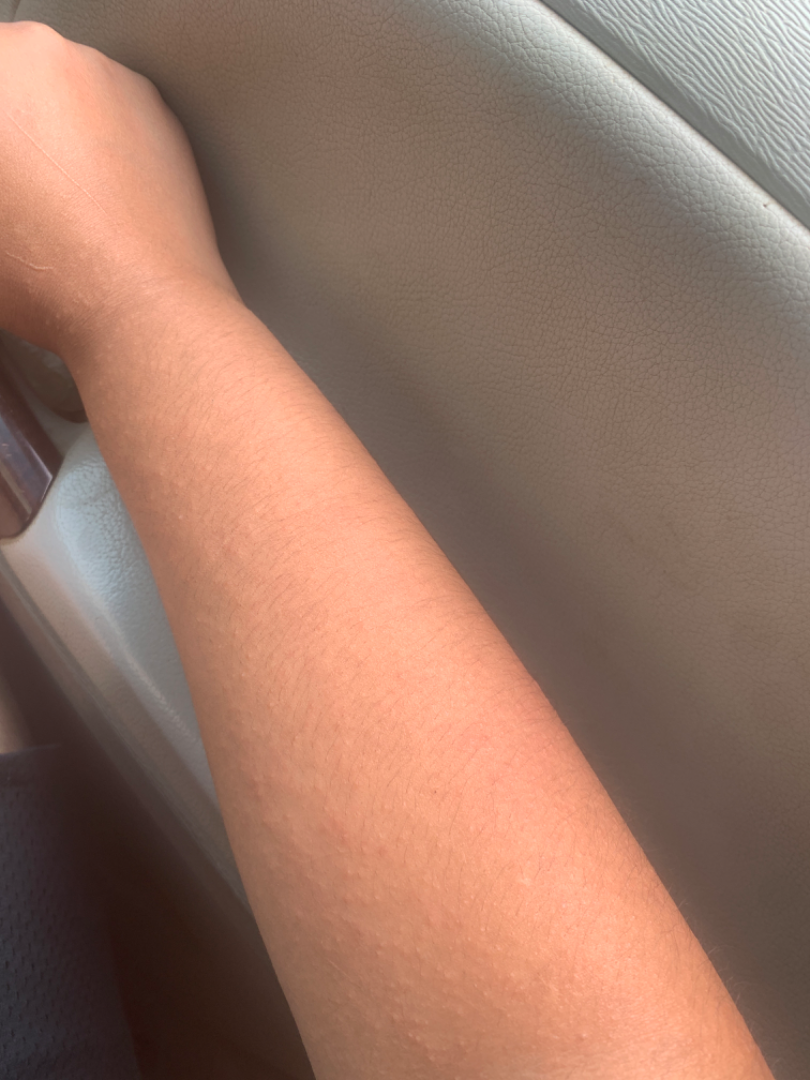lesion texture = raised or bumpy | patient = female, age 18–29 | patient's own categorization = a rash | shot type = at a distance | duration = less than one week | location = arm | reported symptoms = itching | dermatologist impression = most consistent with Keratosis pilaris; the differential also includes Acute dermatitis, NOS; less probable is Folliculitis; a remote consideration is Eczema.